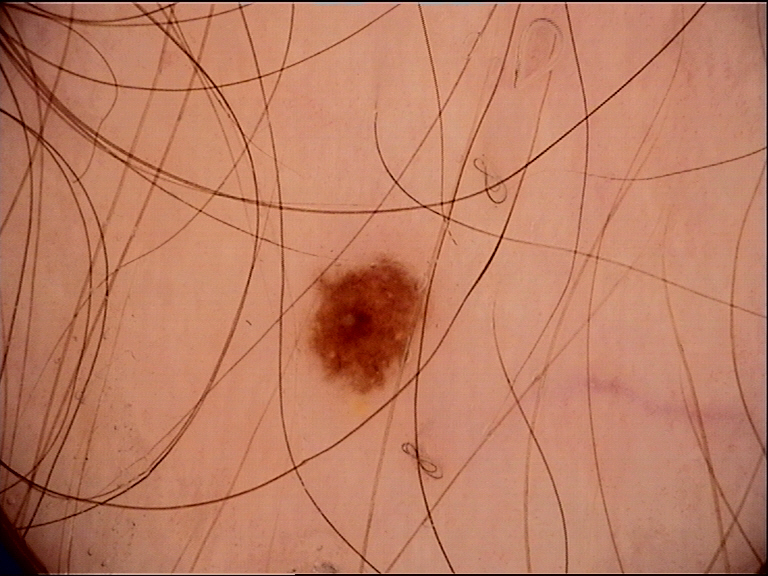Impression: The diagnosis was a dysplastic junctional nevus.